A dermoscopic image of a skin lesion.
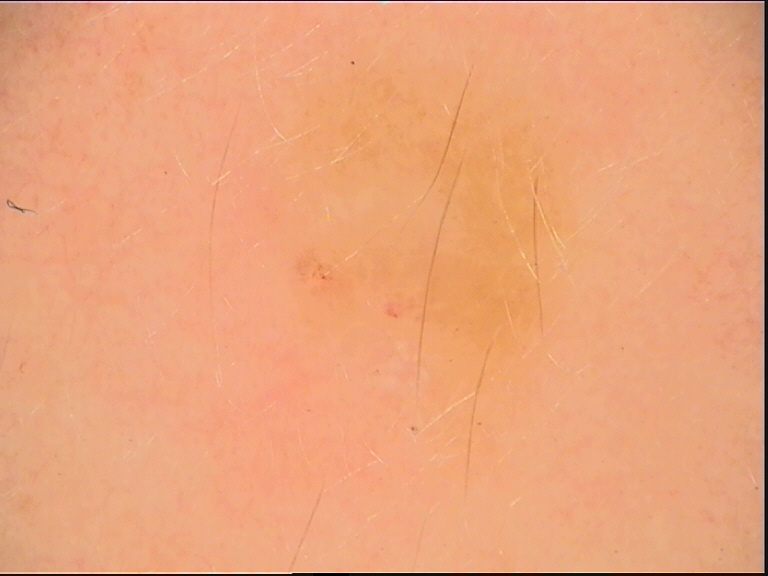Consistent with a dysplastic junctional nevus.